A dermoscopic photograph of a skin lesion.
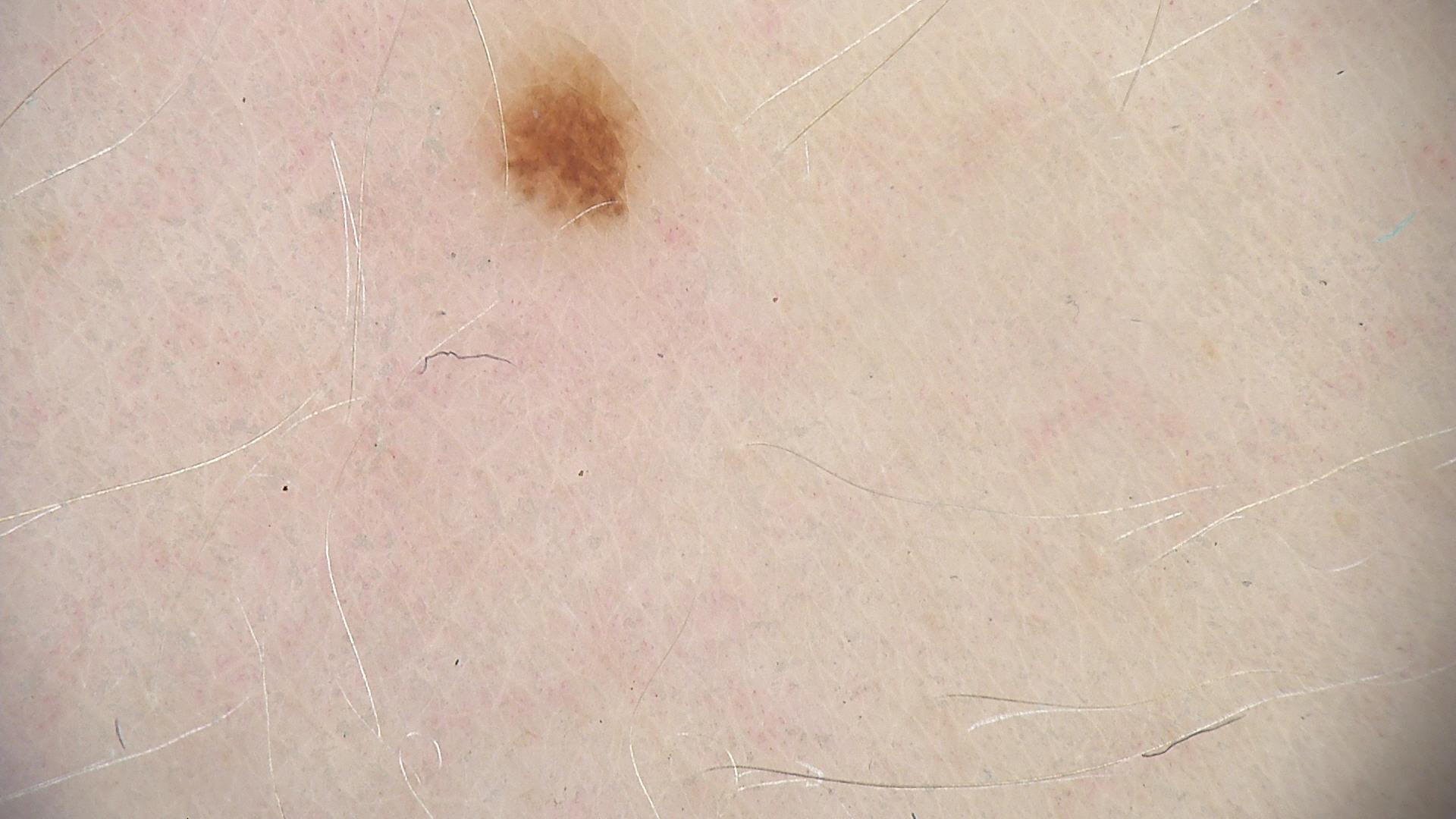assessment = dysplastic junctional nevus (expert consensus)